The photograph was taken at a distance: 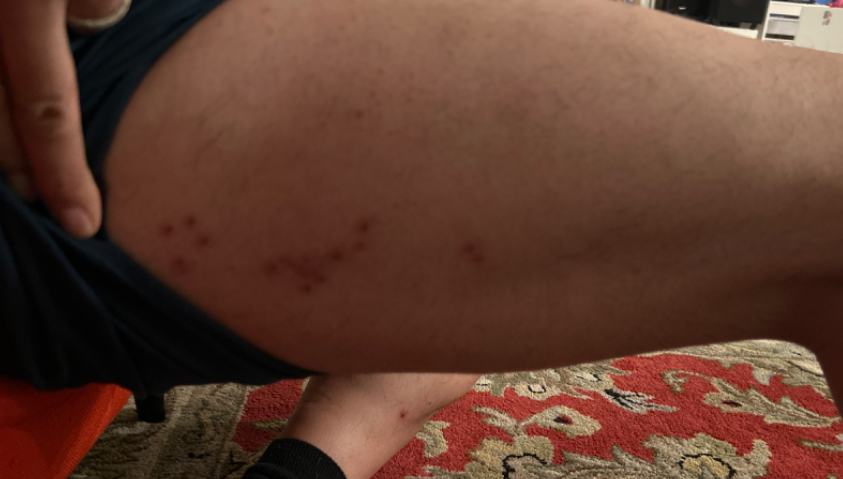{"differential": "Herpes Zoster"}